Recorded as FST III — 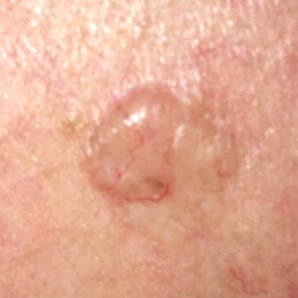The lesion is roughly 9 by 6 mm. Histopathology confirmed a basal cell carcinoma.